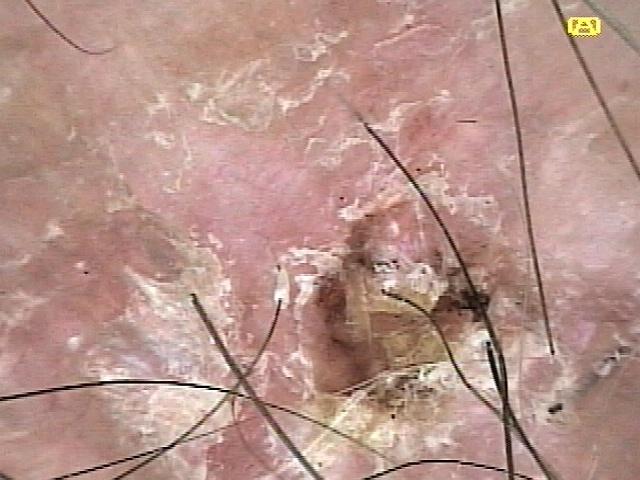patient = male, aged around 85 or older
pathology = Squamous cell carcinoma (biopsy-proven)